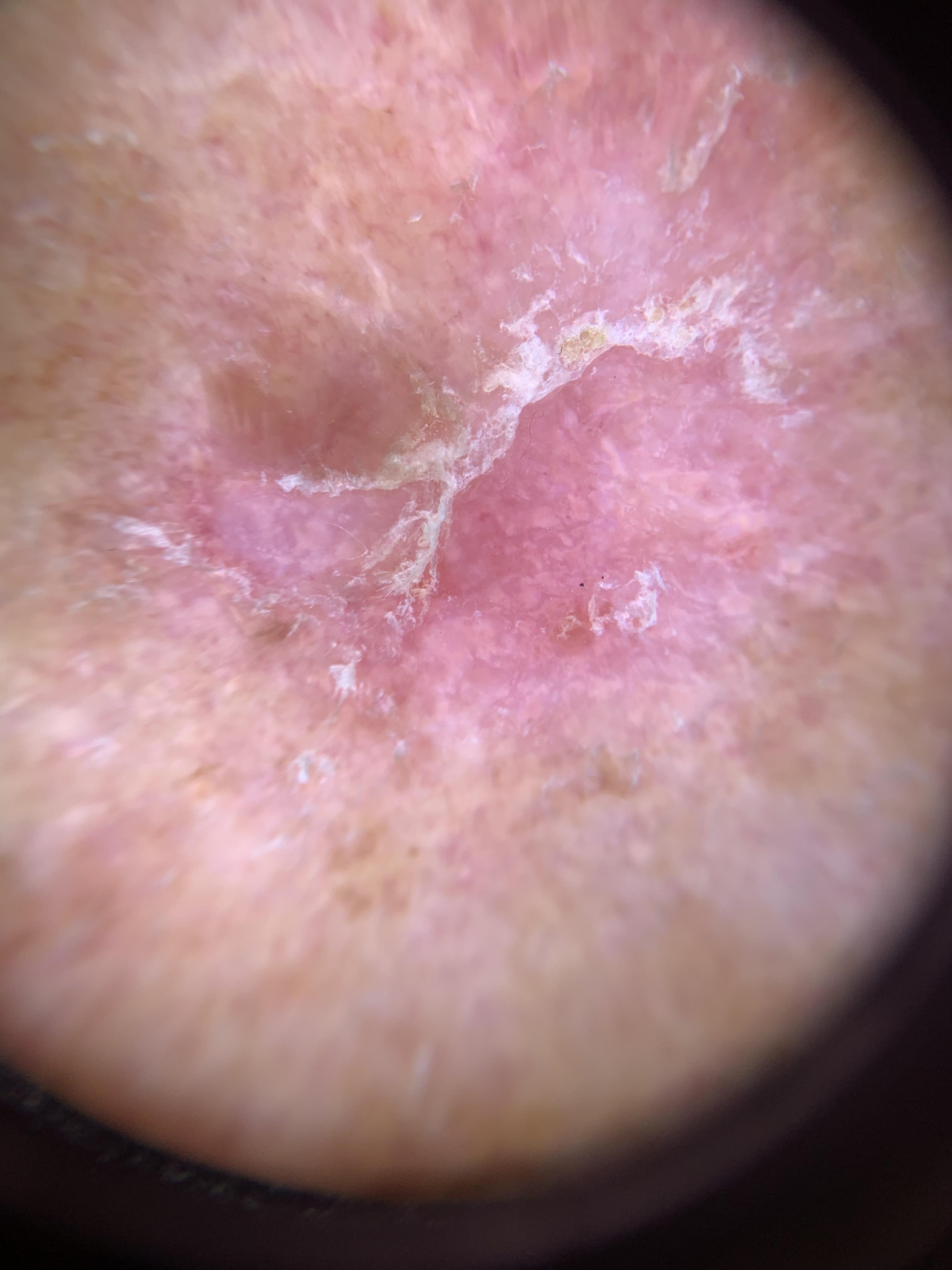{"patient": {"age_approx": 75, "sex": "male"}, "skin_type": "II", "lesion_location": {"region": "the head or neck"}, "diagnosis": {"name": "Solar or actinic keratosis", "malignancy": "indeterminate", "confirmation": "histopathology", "lineage": "epidermal"}}